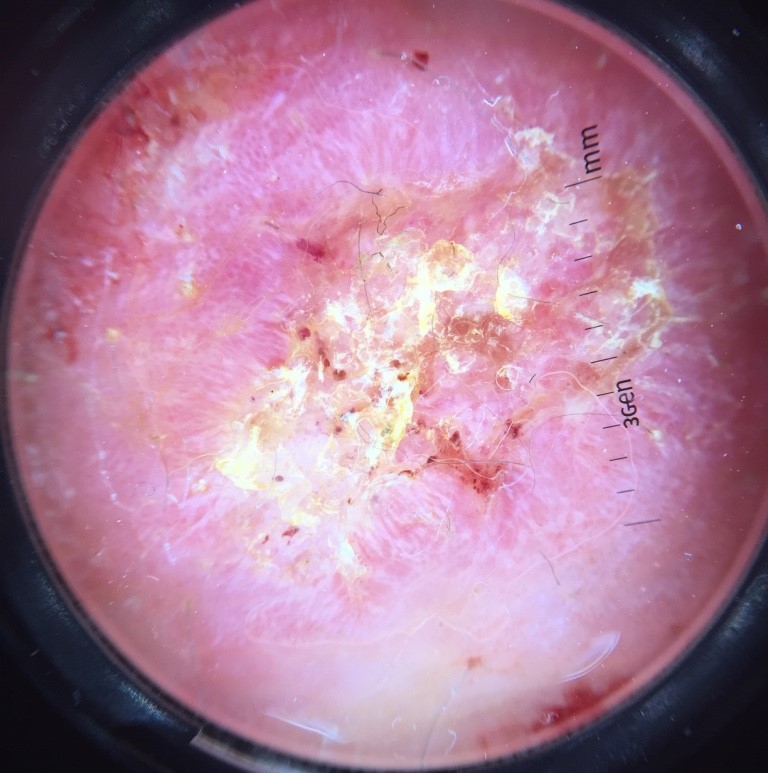A dermoscopic photograph of a skin lesion.
The morphology is that of a keratinocytic lesion.
Biopsy-confirmed as a skin cancer — a squamous cell carcinoma.